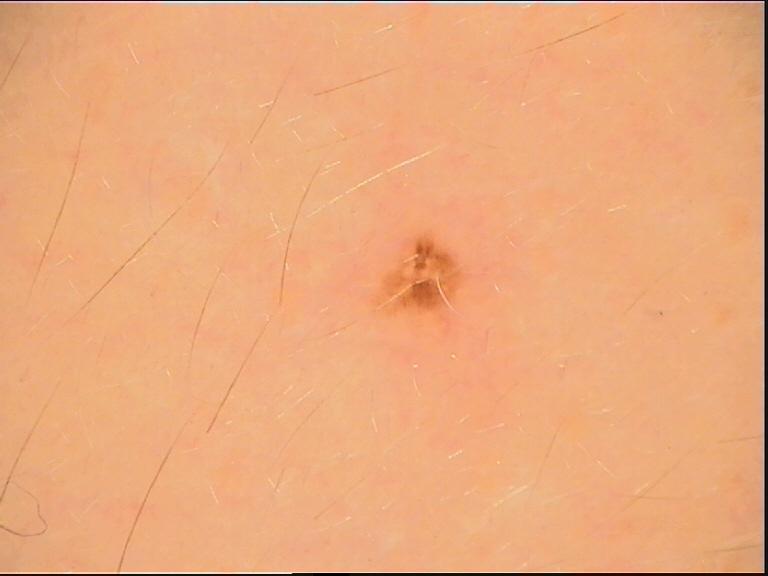Conclusion: Diagnosed as a benign lesion — a dysplastic junctional nevus.